Imaged for a research study, with no referral diagnosis recorded. A female subject 58 years of age. A dermatoscopic image of a skin lesion. On a questionnaire the patient reported a personal history of skin cancer, a family history of skin cancer, and a personal history of cancer. A moderate number of moles by the patient's own estimate — 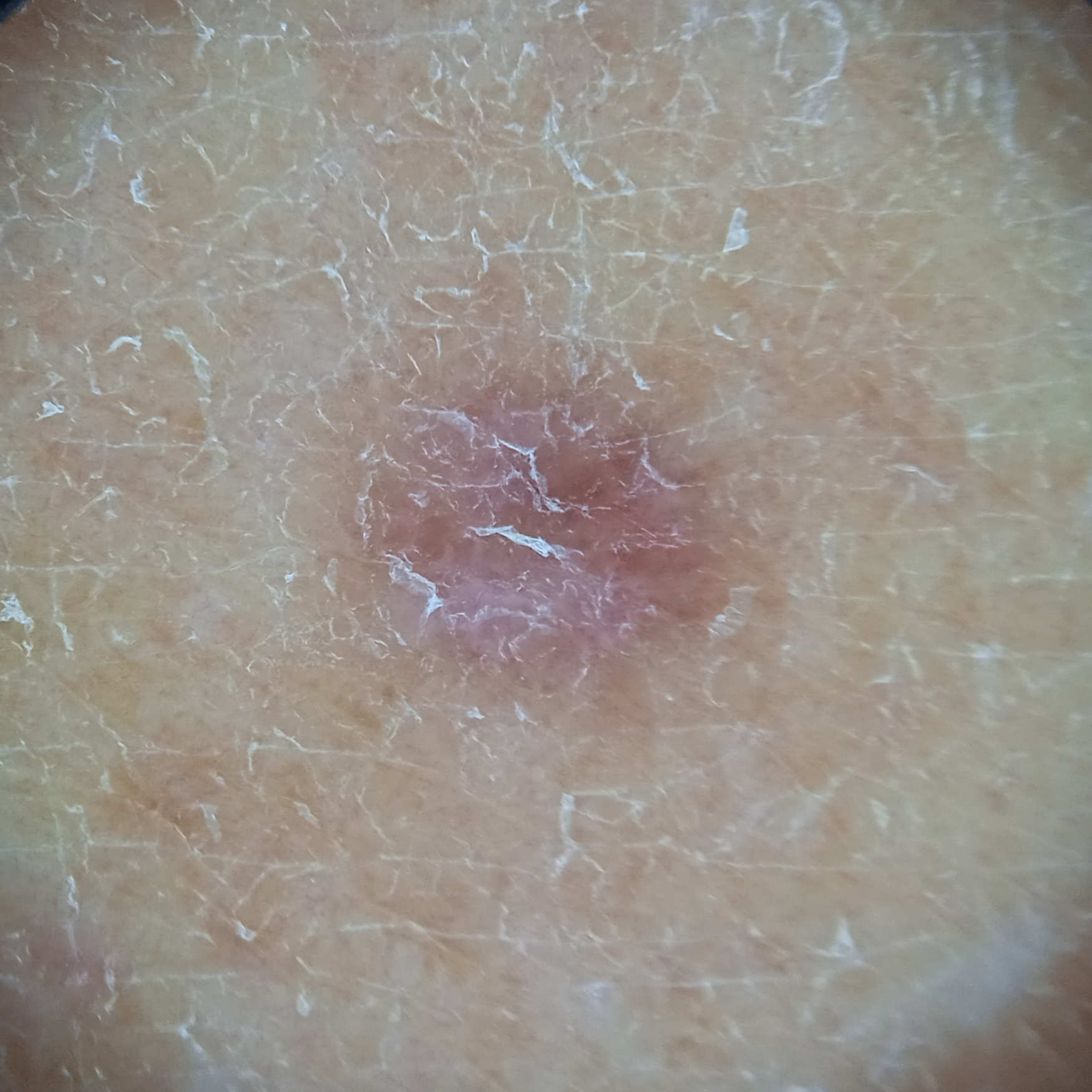Findings:
Located on a leg. Measuring roughly 5.2 mm.
Conclusion:
Dermatologist review favored a dermatofibroma.